Located on the arm; texture is reported as flat; an image taken at an angle; Fitzpatrick skin type II; the patient considered this a rash; the patient indicates the condition has been present for one to four weeks; symptoms reported: enlargement, bothersome appearance and itching — 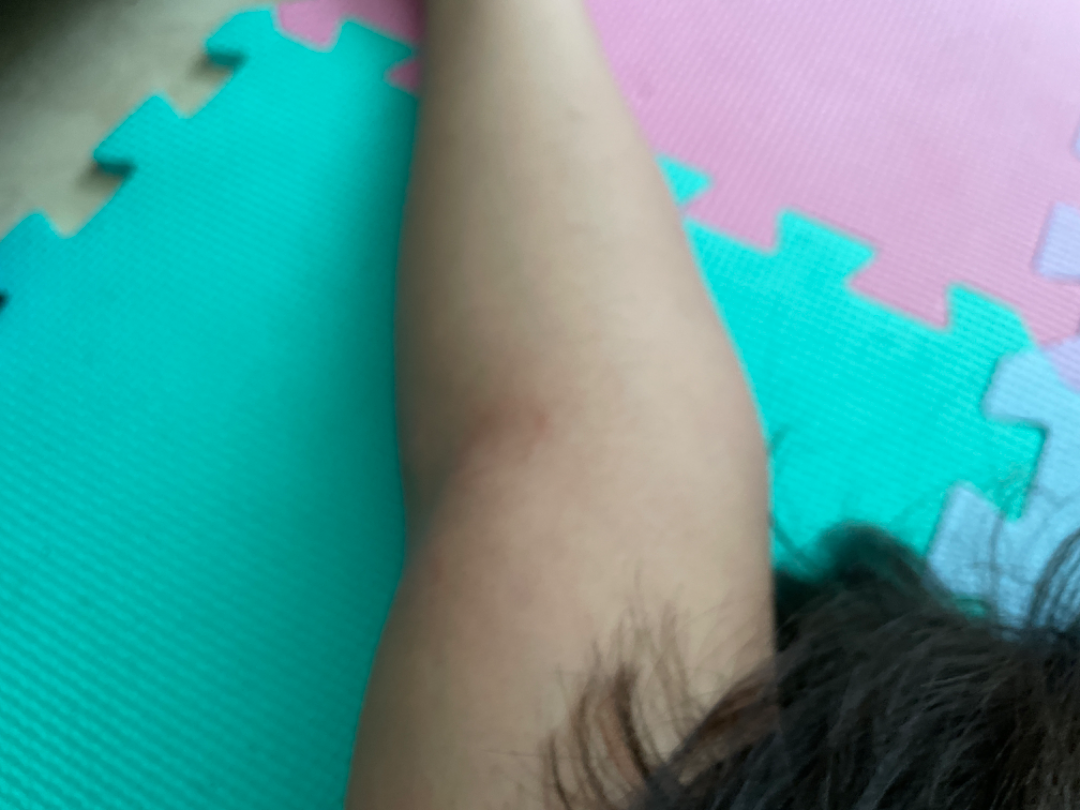Case summary:
* clinical impression — consistent with Eczema